A dermatoscopic image of a skin lesion.
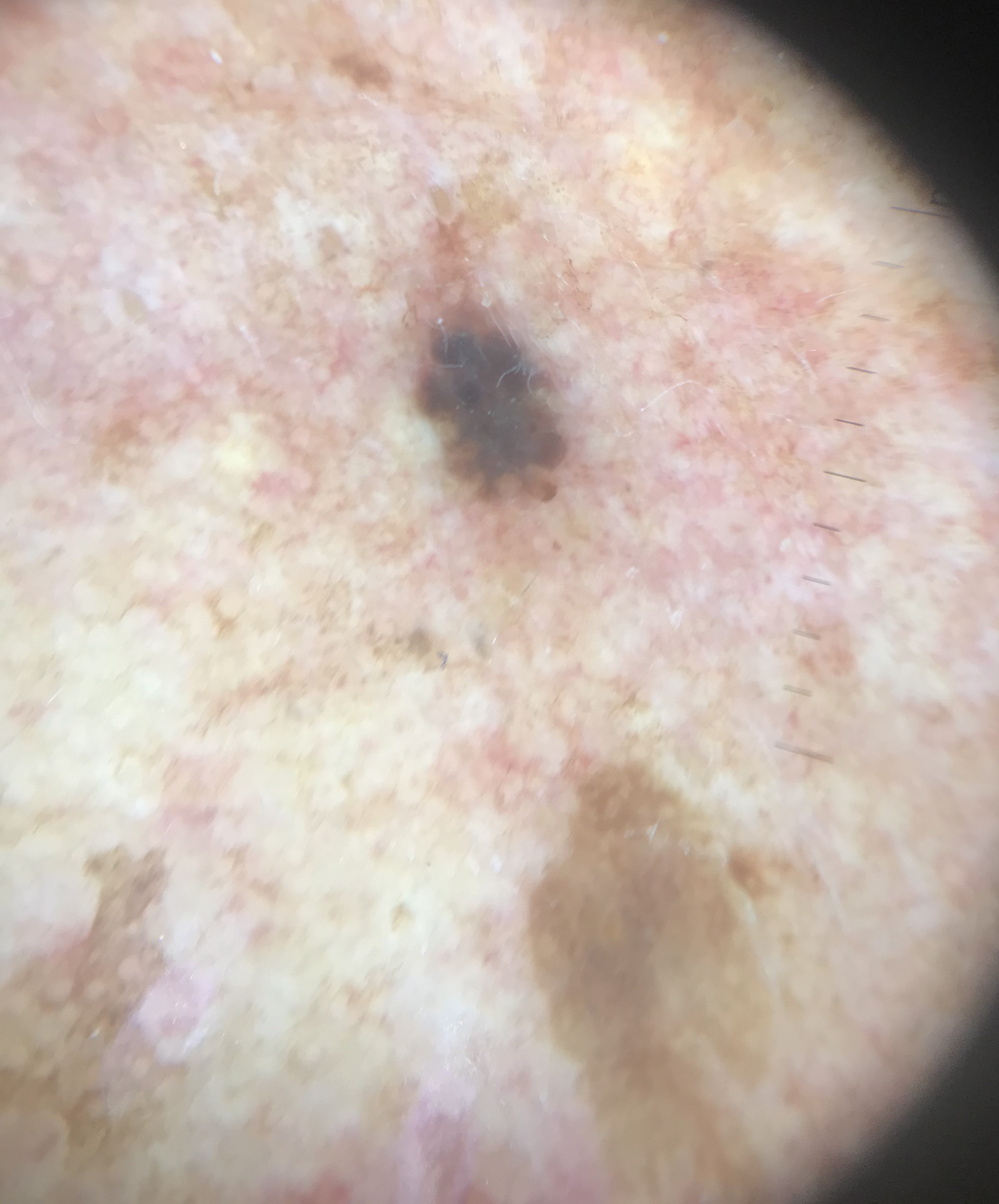Q: What is this lesion?
A: seborrheic keratosis (expert consensus)